By history, prior malignancy (patient or family) · a male subject aged 80 · a clinical photo of a skin lesion taken with a smartphone · Fitzpatrick phototype II:
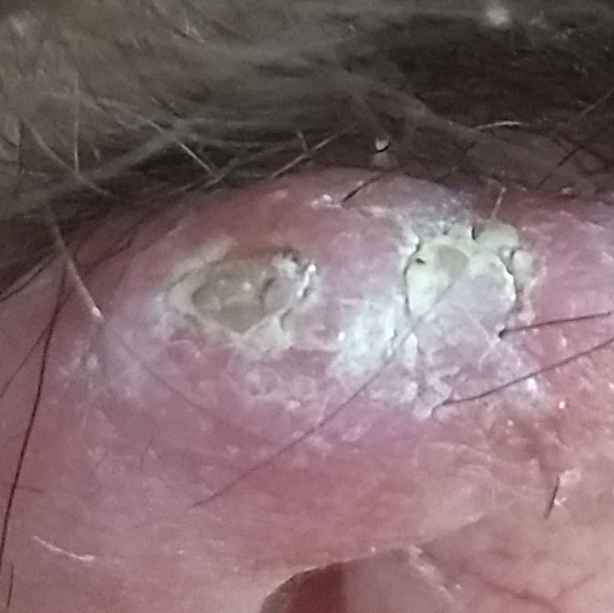Located on an ear.
Measuring about 15 × 10 mm.
By the patient's account, the lesion itches and is elevated.
Biopsy-confirmed as a malignant skin lesion — a squamous cell carcinoma.